A dermoscopic close-up of a skin lesion · the patient is a male aged 58 to 62:
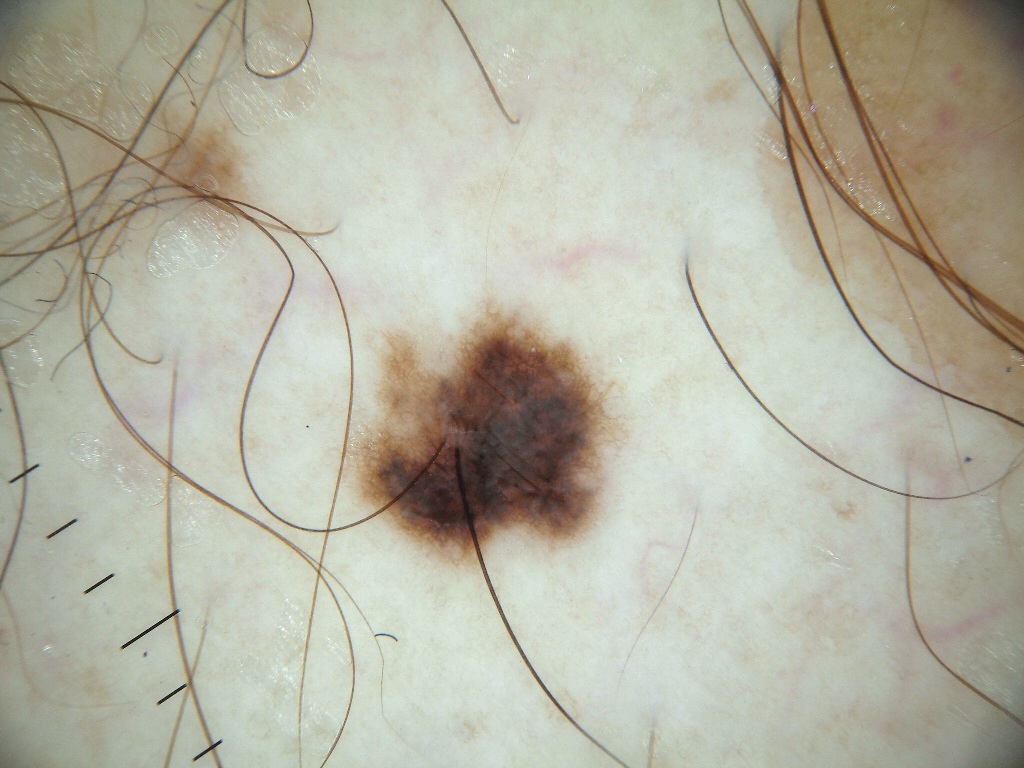features: pigment network
lesion size: moderate
bounding box: 323/296/628/588
assessment: a melanocytic nevus, a benign skin lesion